Texture is reported as raised or bumpy, no associated systemic symptoms reported, skin tone: non-clinician graders estimated 3 on the MST, the photograph was taken at a distance, the contributor notes the condition has been present for one to four weeks, the subject is a female aged 40–49.
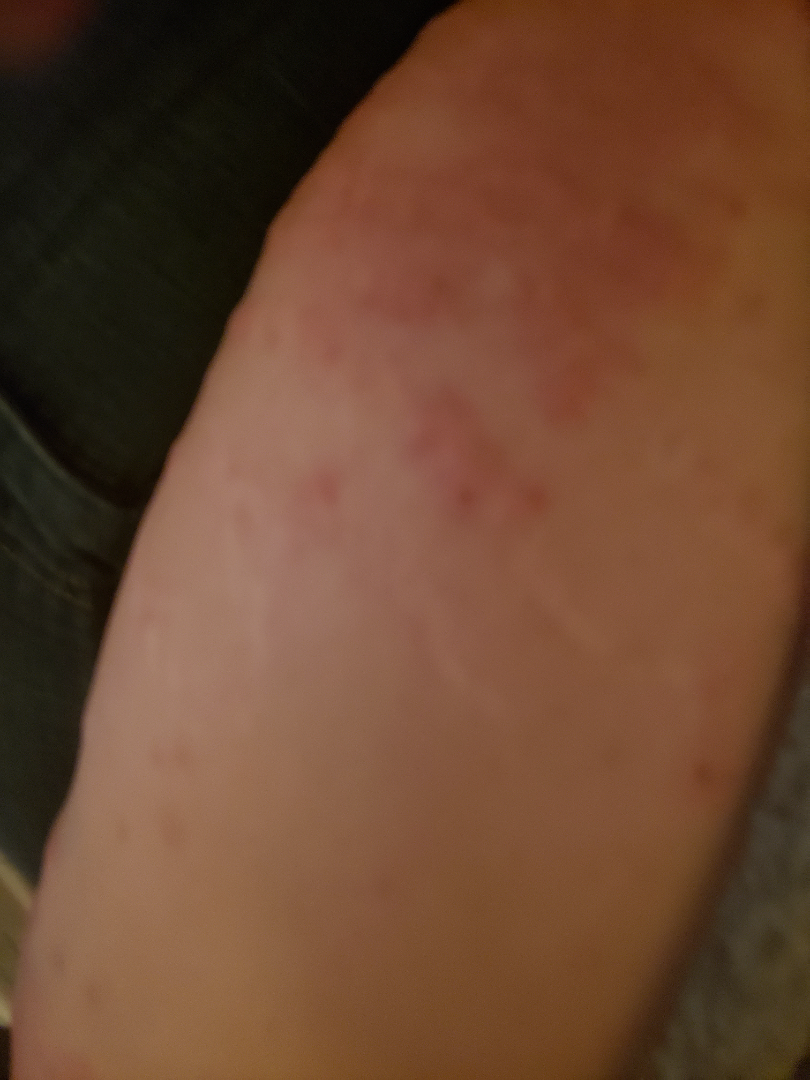Q: Could the case be diagnosed?
A: could not be assessed